A dermoscopy image of a single skin lesion.
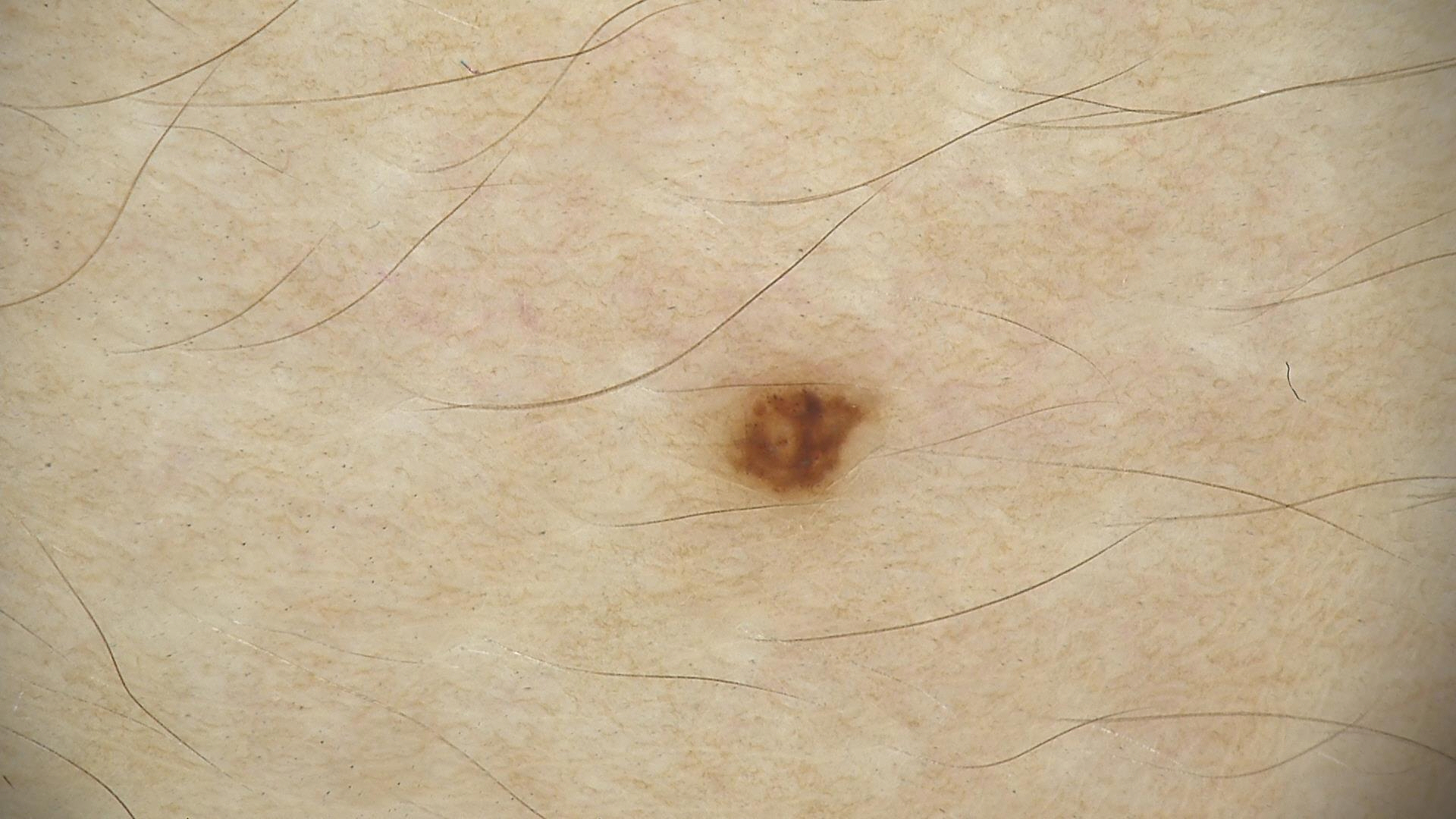Q: What is this lesion?
A: compound nevus (expert consensus)